A female subject in their 50s:
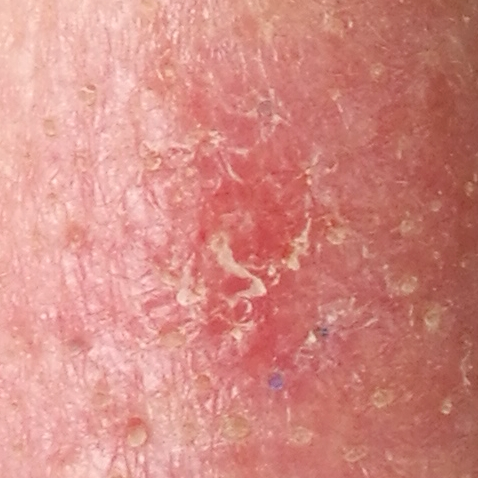The lesion is roughly 6 by 4 mm. Histopathological examination showed a malignancy — a basal cell carcinoma.